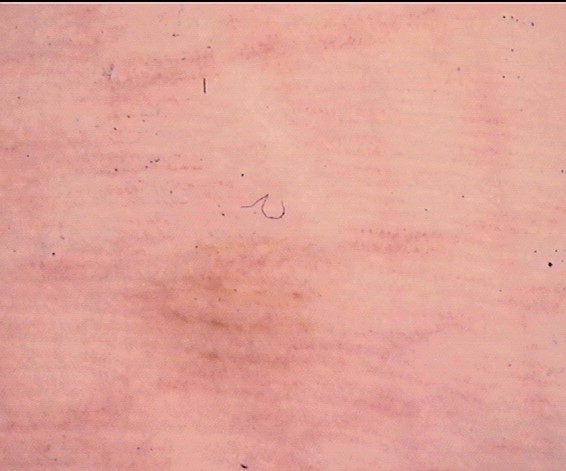modality: dermatoscopy, category: banal, label: acral junctional nevus (expert consensus).